A clinical photograph of a skin lesion · a male subject age 66 · the patient was assessed as skin type II · the chart records tobacco use and pesticide exposure.
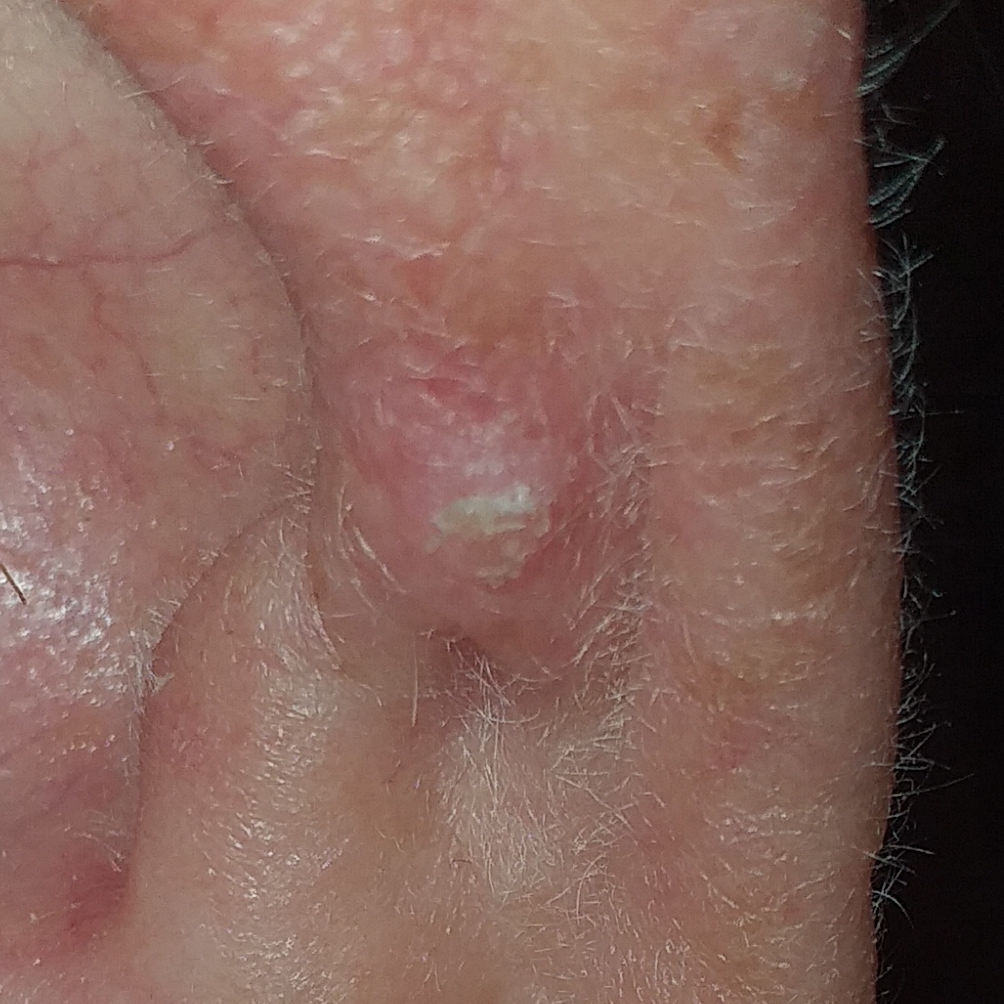• region — an ear
• lesion size — approx. 4 × 3 mm
• diagnosis — squamous cell carcinoma (biopsy-proven)